A dermoscopic image of a skin lesion: 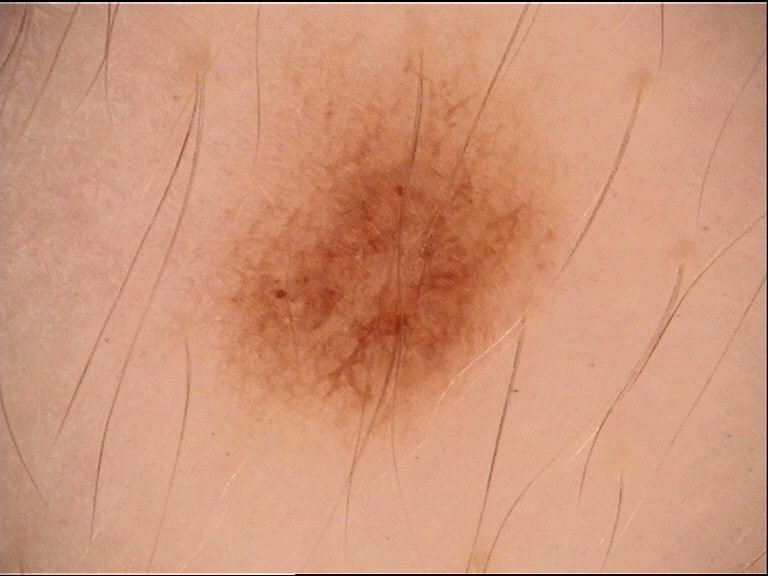<case>
<diagnosis>
<name>dysplastic junctional nevus</name>
<code>jd</code>
<malignancy>benign</malignancy>
<super_class>melanocytic</super_class>
<confirmation>expert consensus</confirmation>
</diagnosis>
</case>